A male patient aged 48 to 52 · a contact-polarized dermoscopy image of a skin lesion · the patient was assessed as skin type II: 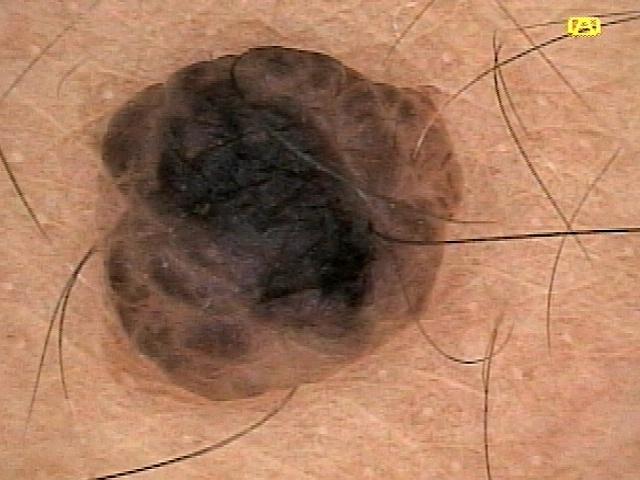Notes:
– site · the trunk
– diagnostic label · Nevus (clinical impression)